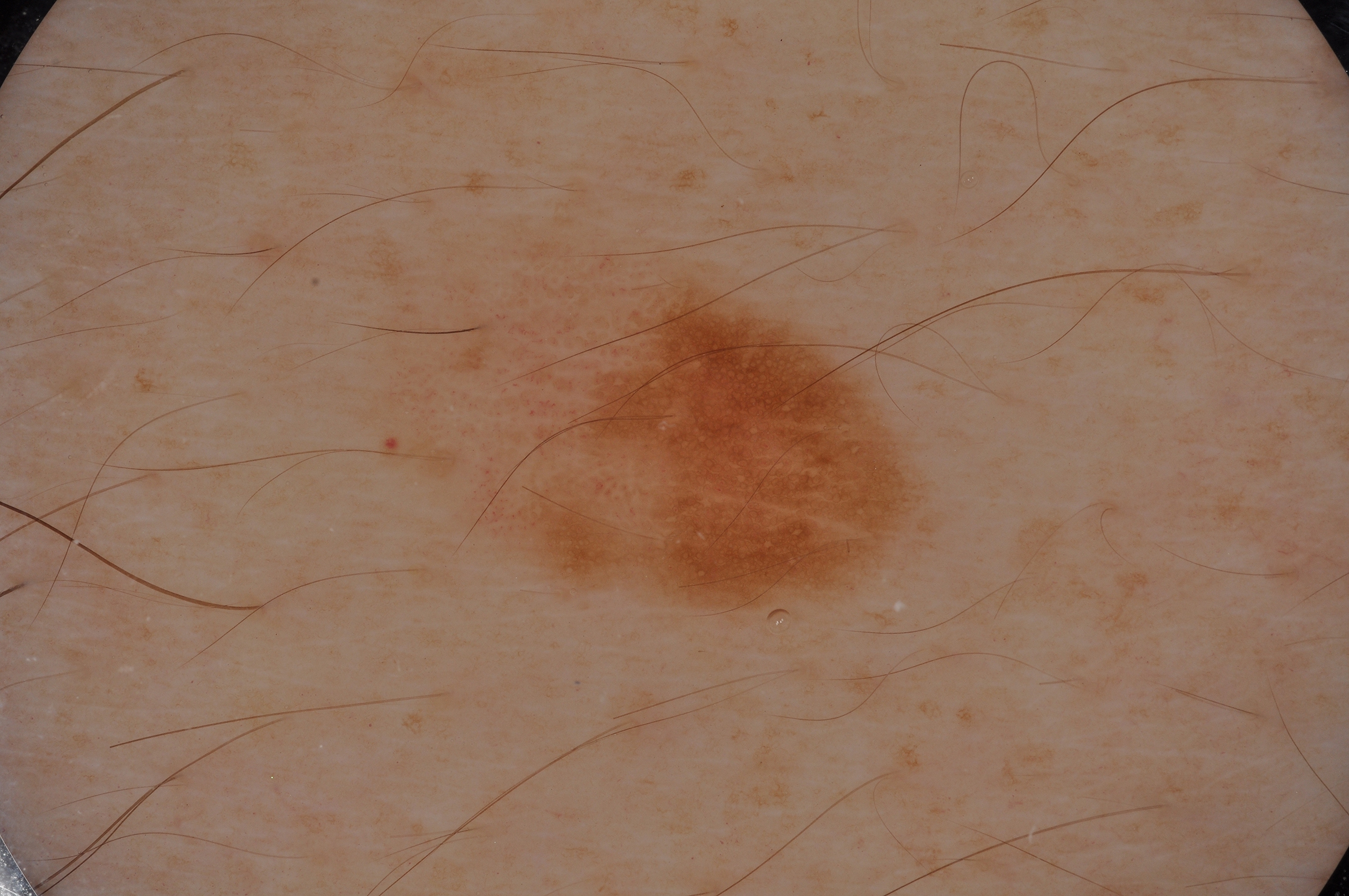Image and clinical context: A dermoscopic close-up of a skin lesion. A male patient, in their 40s. A mid-sized lesion within the field. As (left, top, right, bottom), the lesion is bounded by 361, 211, 944, 625. Dermoscopy demonstrates negative network and pigment network; no streaks or milia-like cysts. Diagnosis: Histopathological examination showed a melanoma, a malignant skin lesion.